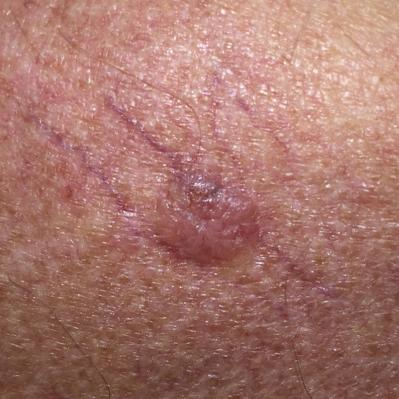Q: What is the imaging modality?
A: clinical photo
Q: What is the patient's skin type?
A: II
Q: Tell me about the patient.
A: male, age 44
Q: Any relevant history?
A: pesticide exposure, prior skin cancer (patient or family)
Q: Where on the body is the lesion?
A: the back
Q: What are the lesion's dimensions?
A: 11x9 mm
Q: What is the diagnosis?
A: basal cell carcinoma (biopsy-proven)